Contact-polarized dermoscopy of a skin lesion; a male patient aged approximately 40:
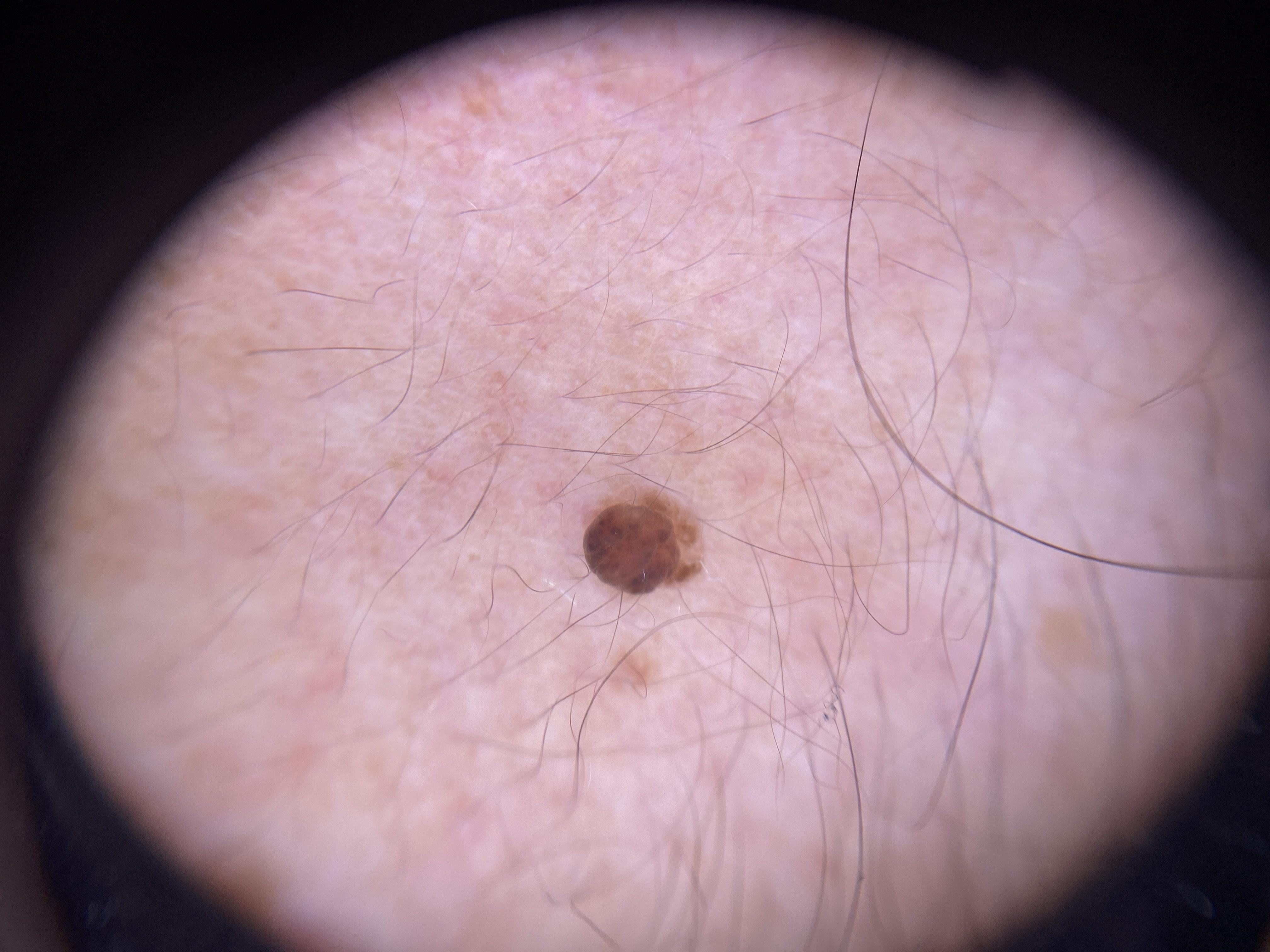Located on the head or neck. Histopathological examination showed a nevus.